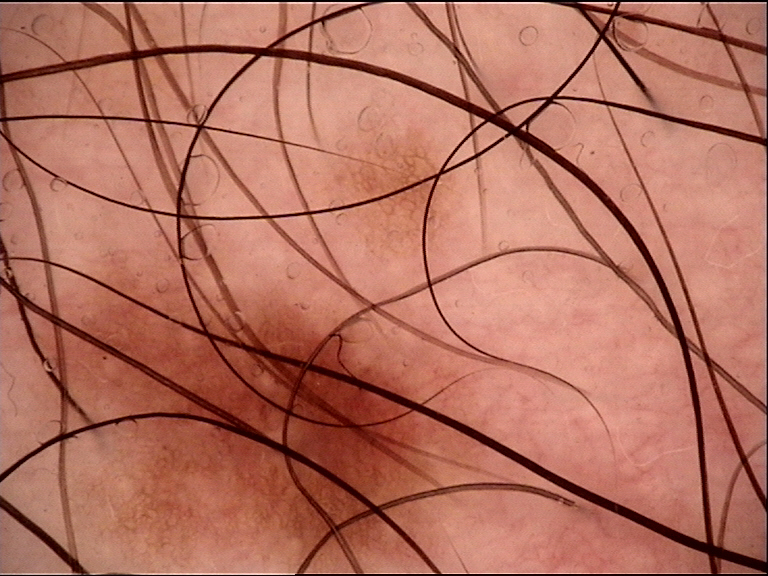Q: What is this lesion?
A: dysplastic junctional nevus (expert consensus)